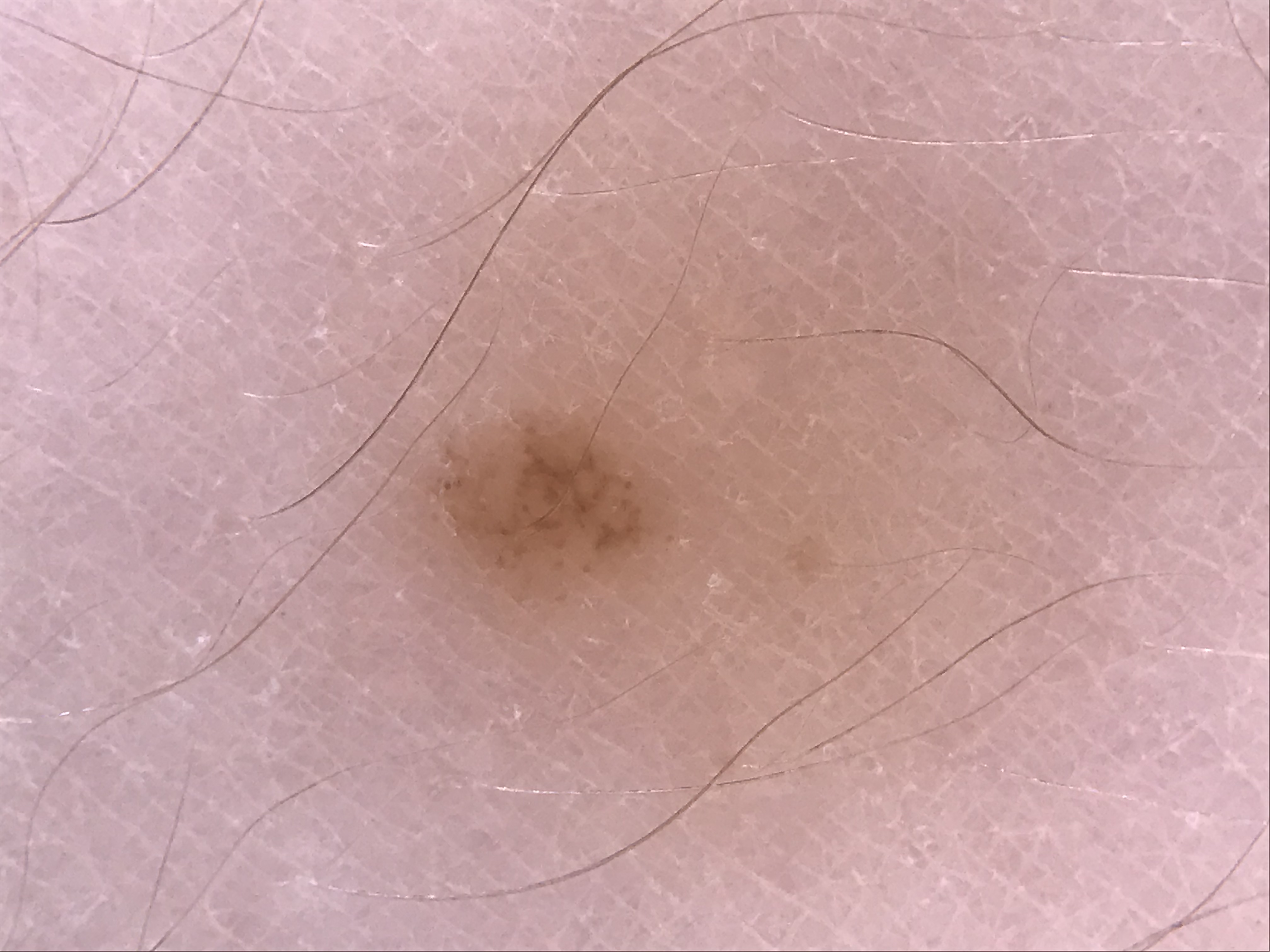Impression: Labeled as a dysplastic junctional nevus.